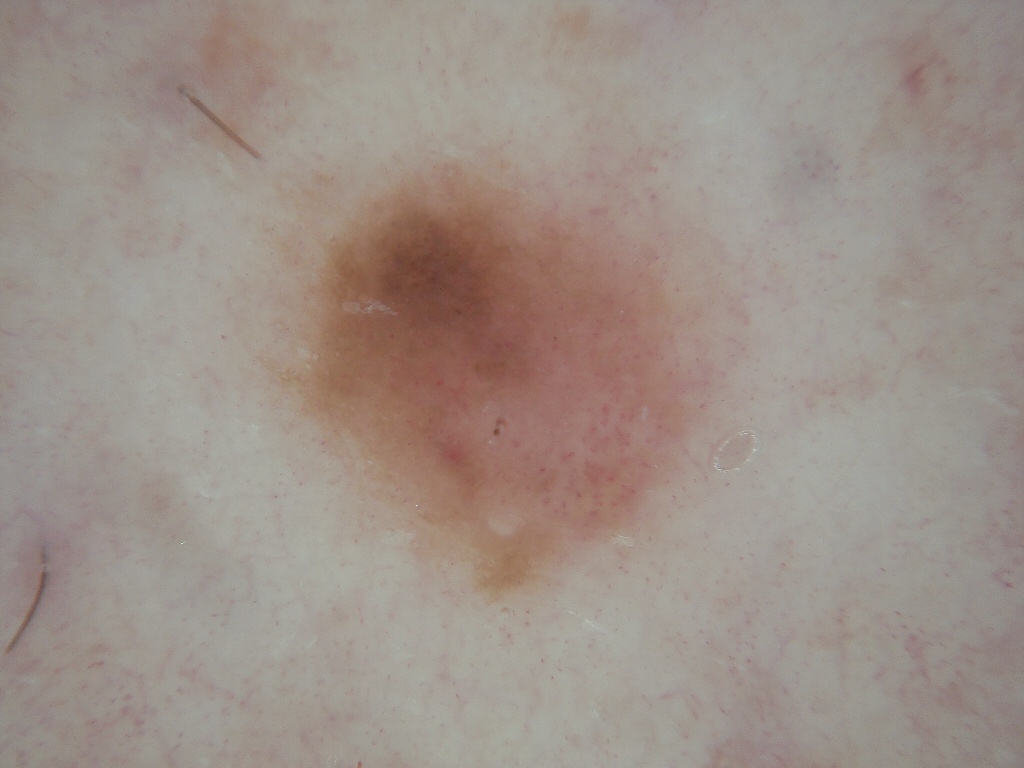Summary: The subject is a female in their mid- to late 50s. A dermoscopy image of a single skin lesion. The lesion is bounded by x1=259, y1=151, x2=714, y2=601. Dermoscopic examination shows pigment network. A mid-sized lesion within the field. Assessment: Clinically diagnosed as a melanocytic nevus.